The patient is a male roughly 60 years of age; a dermatoscopic image of a skin lesion.
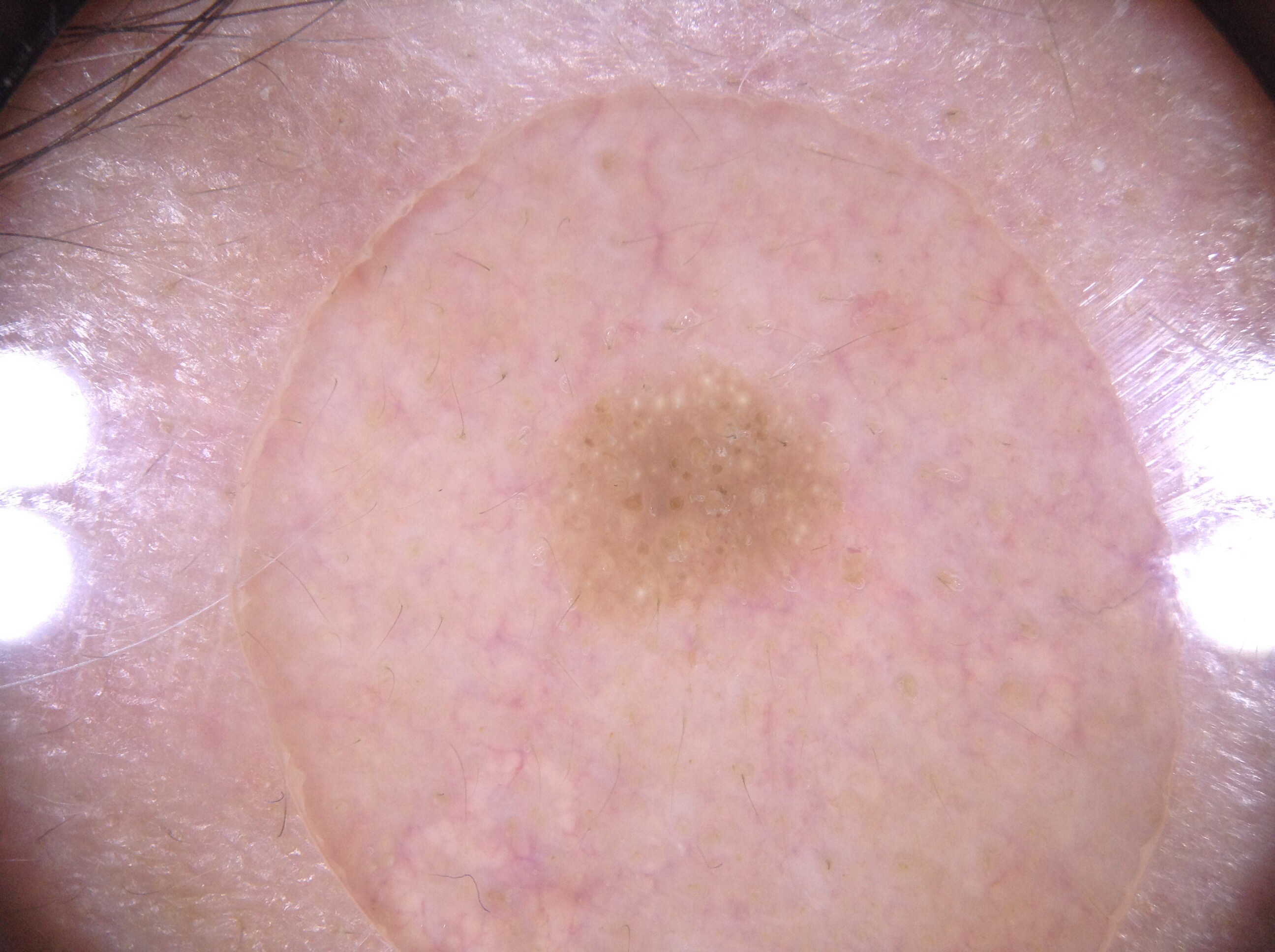features: milia-like cysts | extent: ~5% of the field | lesion bbox: bbox(518, 353, 884, 668) | impression: a seborrheic keratosis, a lesion of keratinocytic origin.